The subject is a male aged 30–39, close-up view, the affected area is the arm and leg:
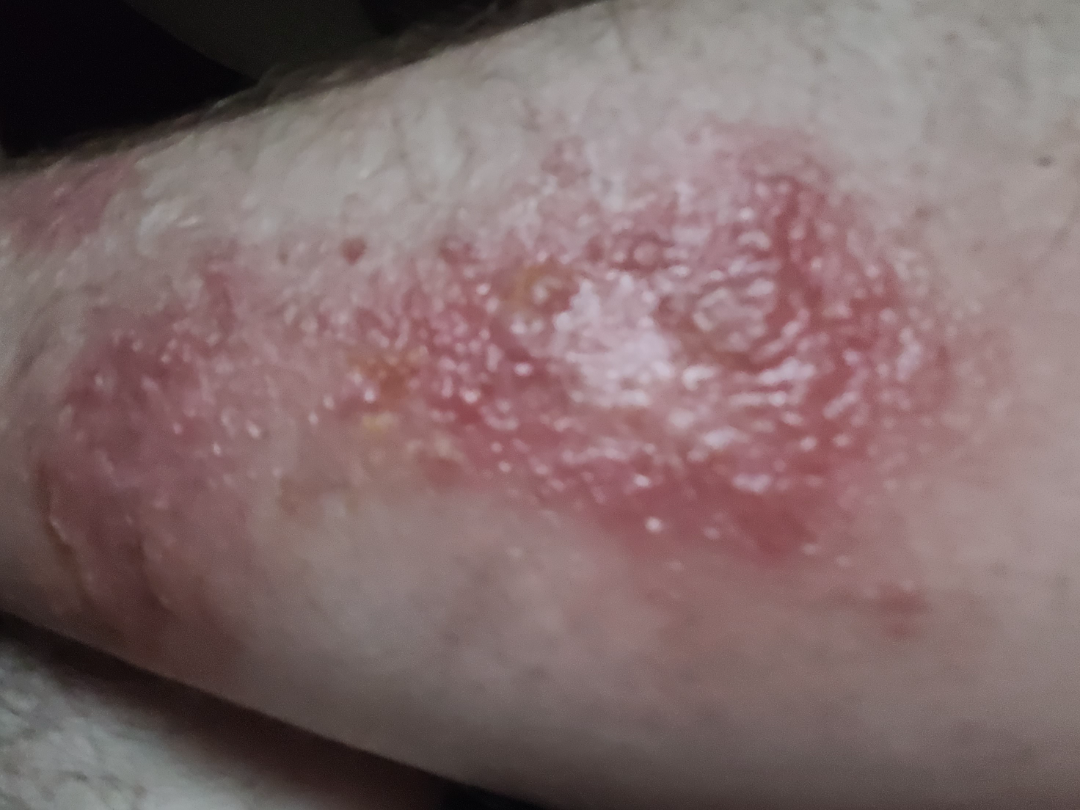assessment: indeterminate